A dermoscopic close-up of a skin lesion.
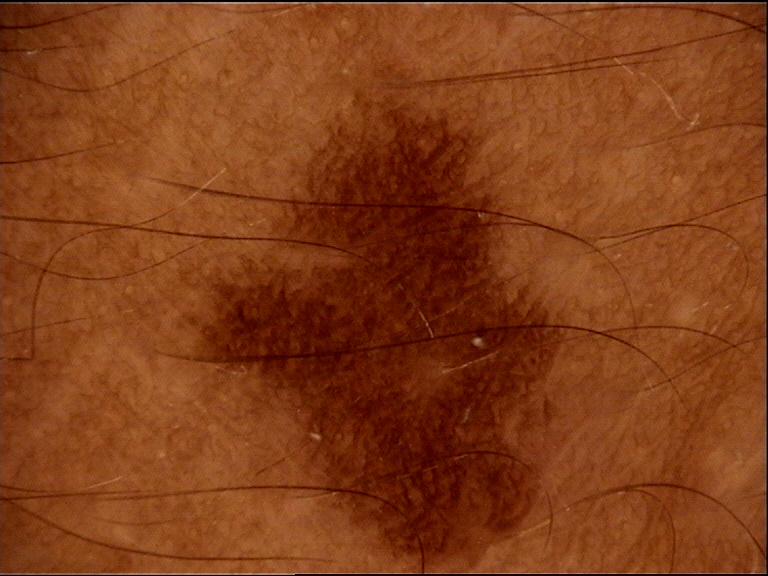label: dysplastic junctional nevus (expert consensus)